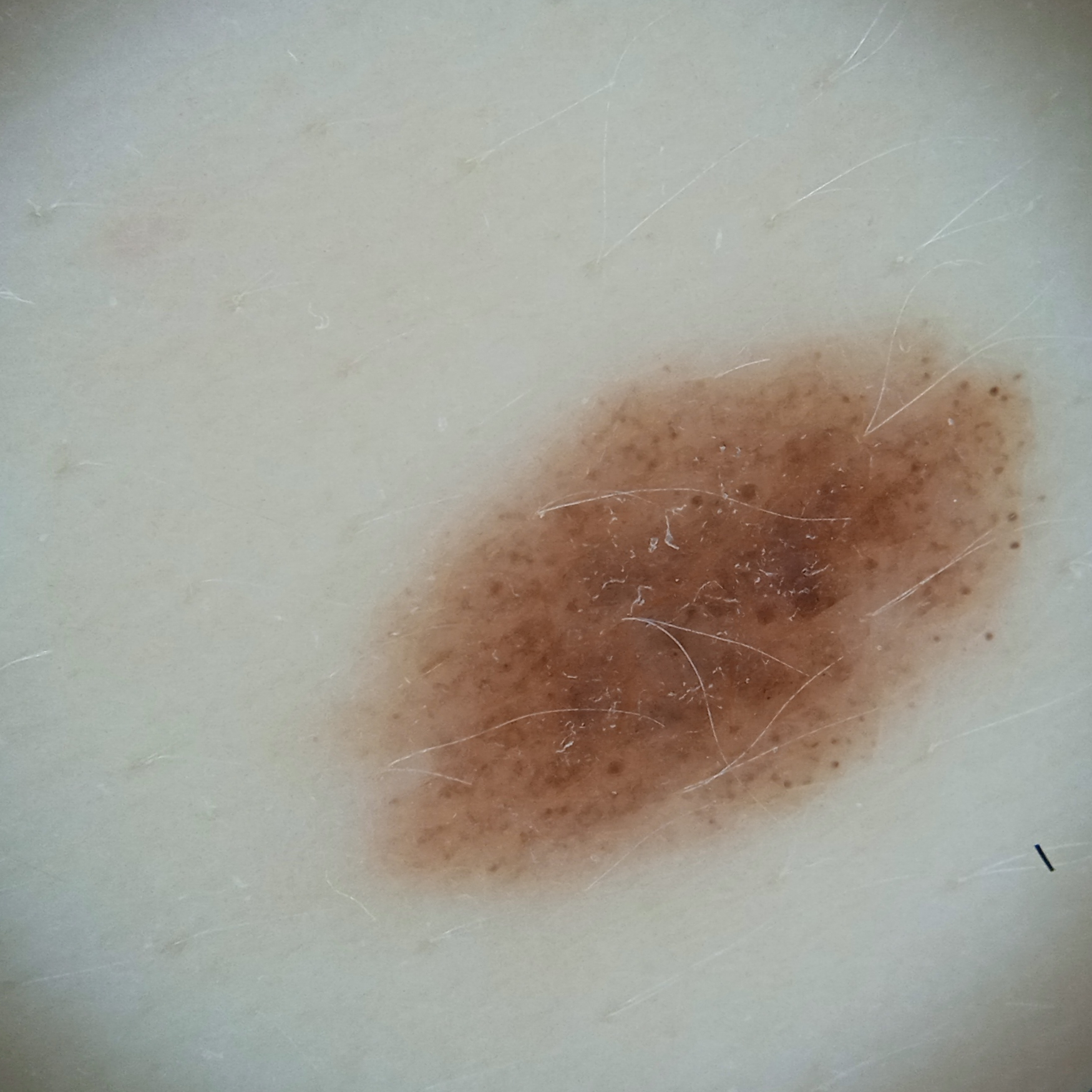Dermoscopy of a skin lesion. A female subject 27 years of age. The lesion is located on the back. The lesion measures approximately 9.4 mm. The dermatologists' assessment was a melanocytic nevus.